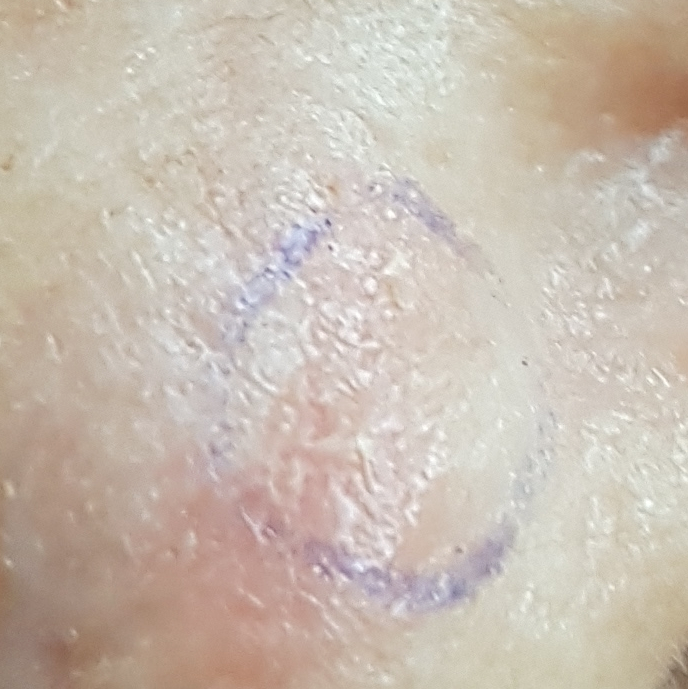imaging — smartphone clinical photo
site — the nose
impression — actinic keratosis (clinical consensus)